Imaged for a research study, with no referral diagnosis recorded; the patient describes having a moderate number of moles; a dermatoscopic image of a skin lesion: 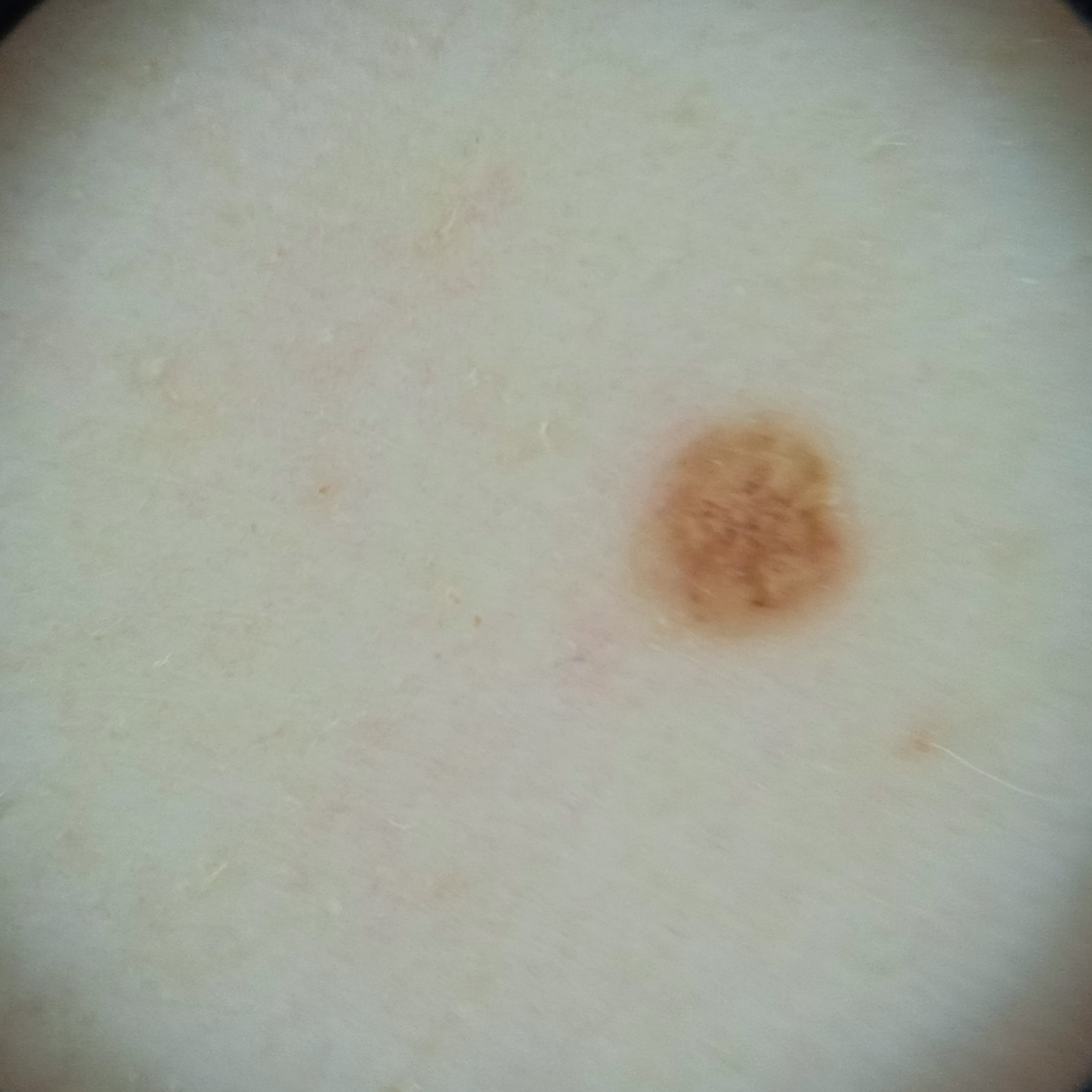  lesion_location: the back
  lesion_size:
    diameter_mm: 2.2
  diagnosis:
    name: melanocytic nevus
    malignancy: benign